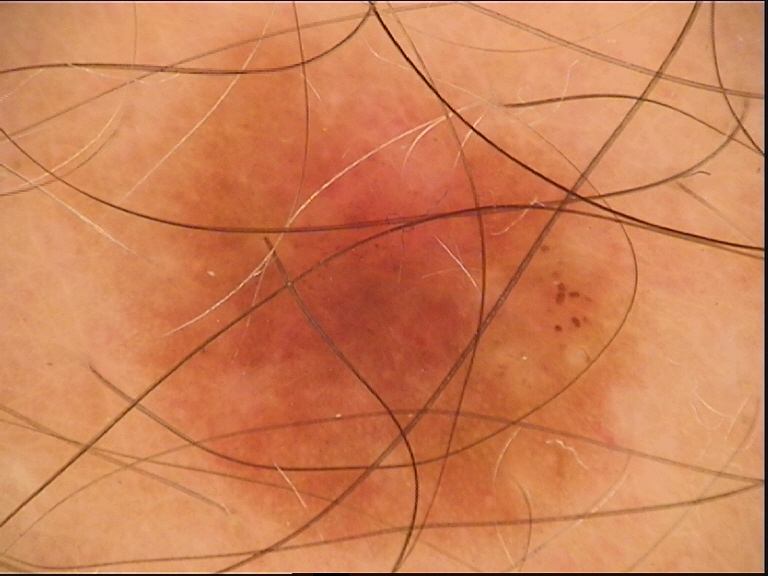Q: What kind of lesion is this?
A: banal
Q: What was the diagnostic impression?
A: compound nevus (expert consensus)